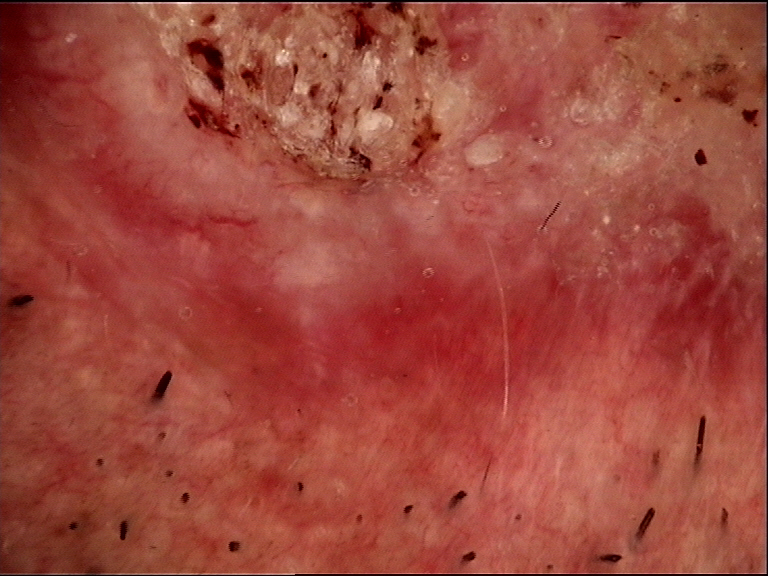{"image": "dermatoscopy", "lesion_type": {"main_class": "keratinocytic"}, "diagnosis": {"name": "squamous cell carcinoma", "code": "scc", "malignancy": "malignant", "super_class": "non-melanocytic", "confirmation": "histopathology"}}